The patient is a male aged 13 to 17 · a dermoscopic close-up of a skin lesion — 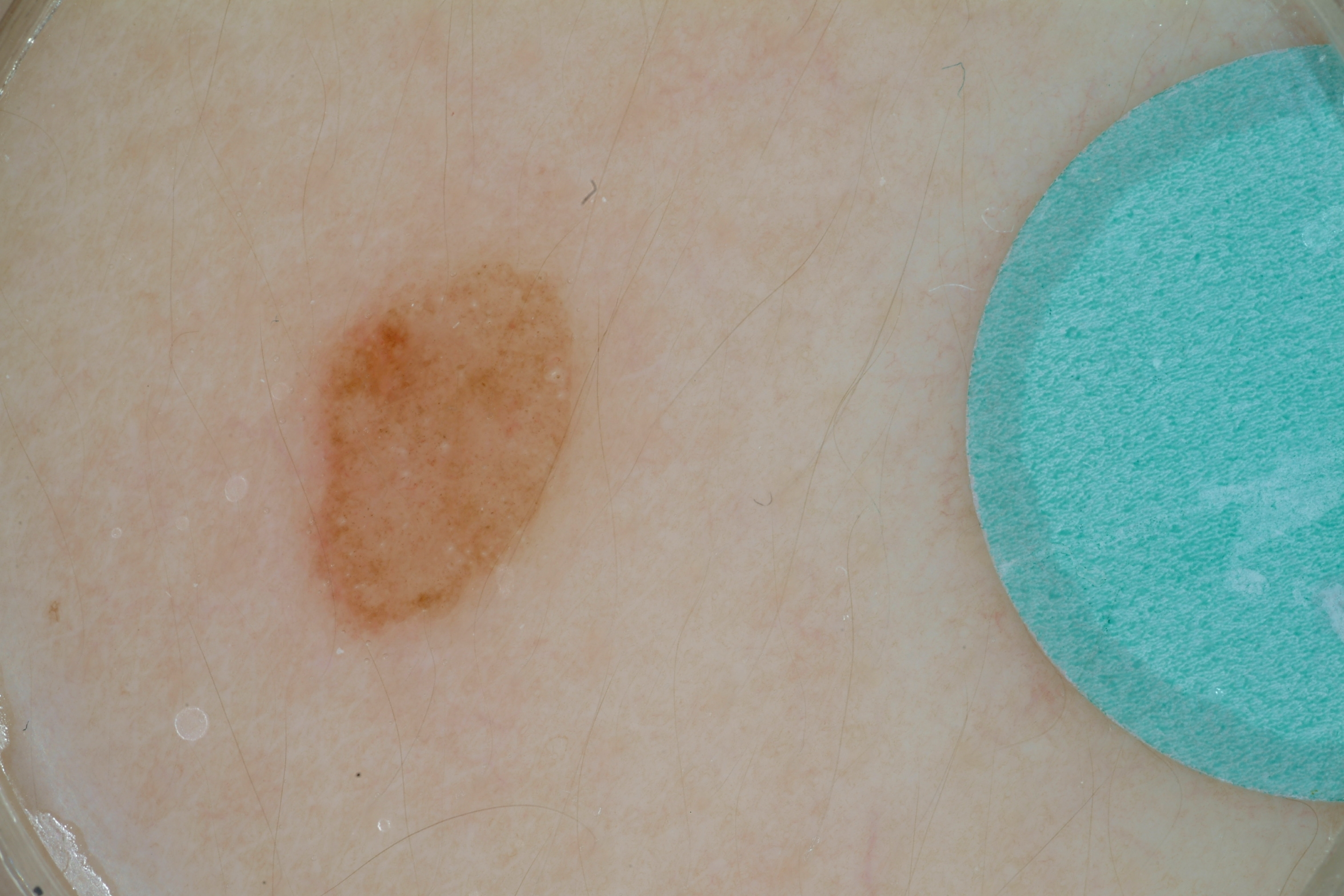Case summary: The lesion occupies the region 299/257/579/621. Dermoscopic examination shows milia-like cysts; no streaks, negative network, globules, or pigment network. Assessment: Expert review diagnosed this as a melanocytic nevus, a benign lesion.